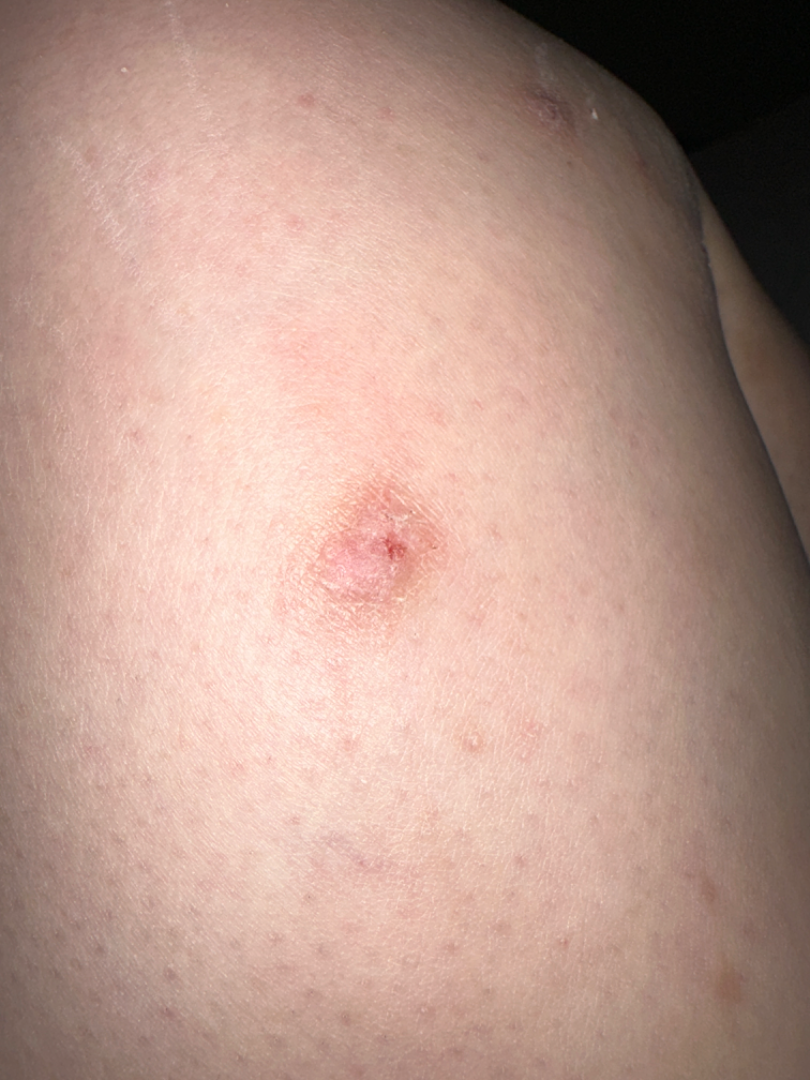Q: Could the case be diagnosed?
A: indeterminate
Q: Where on the body?
A: leg
Q: Patient demographics?
A: female, age 30–39
Q: How long has this been present?
A: since childhood
Q: How was the photo taken?
A: close-up
Q: Any systemic symptoms?
A: none reported
Q: What symptoms does the patient report?
A: itching